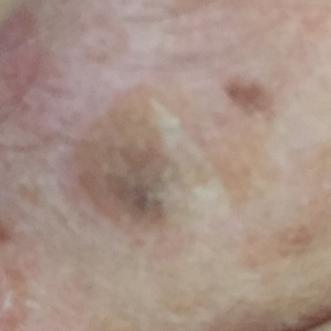| key | value |
|---|---|
| image type | clinical photo |
| subject | age 68 |
| body site | an ear |
| reported symptoms | elevation / no itching, no pain |
| diagnosis | seborrheic keratosis (clinical consensus) |